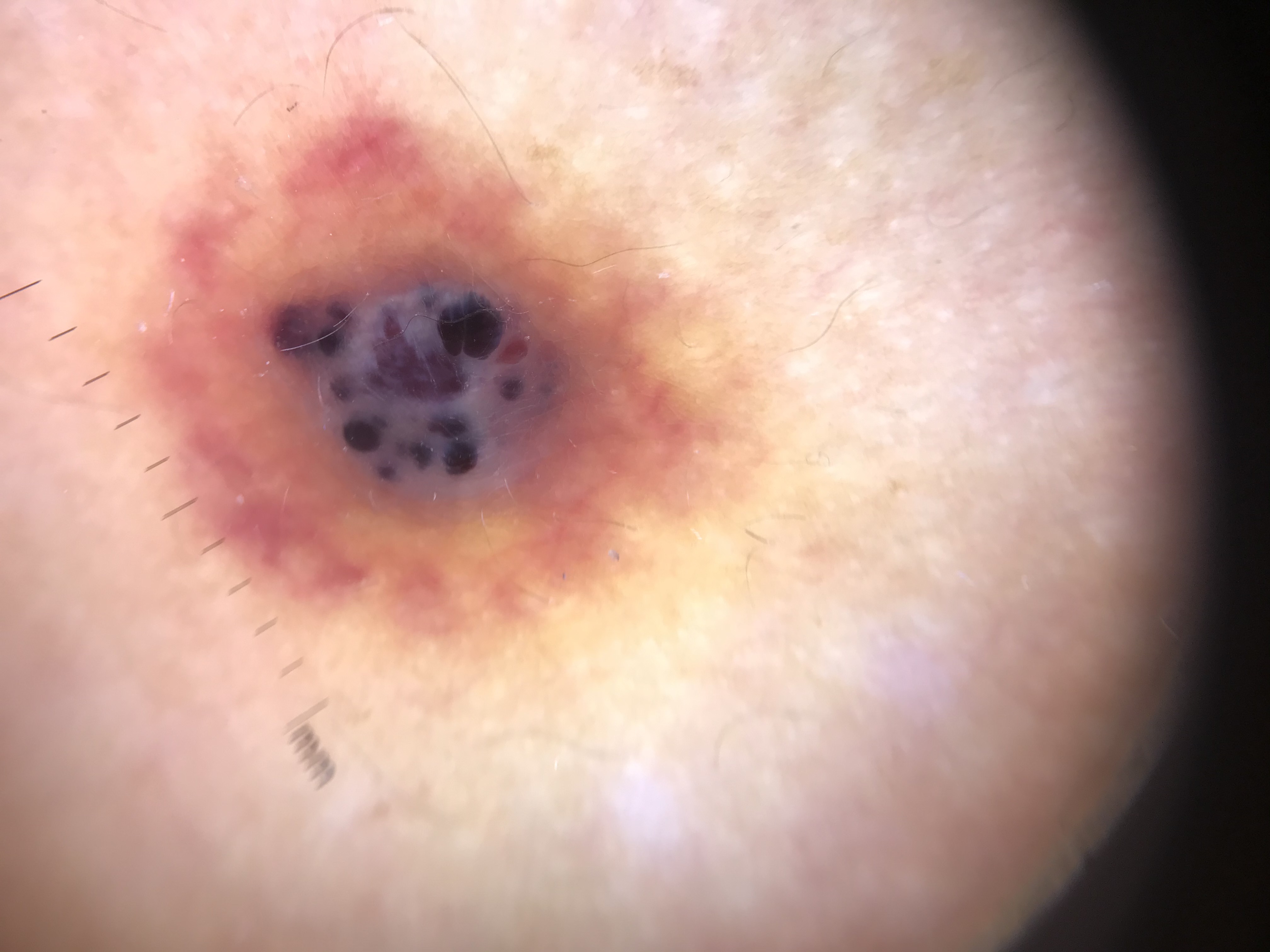Classified as an angiokeratoma.